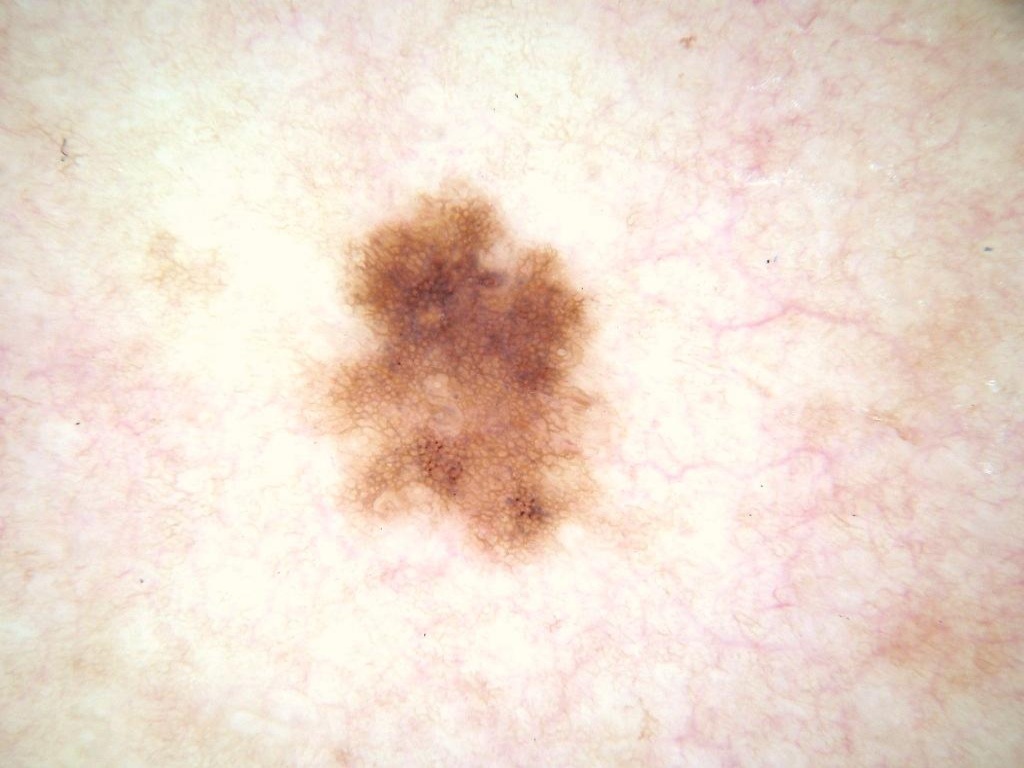Image and clinical context: A dermoscopic image of a skin lesion. The patient is a female aged 48 to 52. The dermoscopic pattern shows milia-like cysts and pigment network, with no streaks, globules, or negative network. A moderately sized lesion. In (x1, y1, x2, y2) order, lesion location: box(293, 172, 648, 569). Impression: Diagnosed as a melanocytic nevus.